The subject is a female aged 40–49; a close-up photograph; the head or neck is involved — 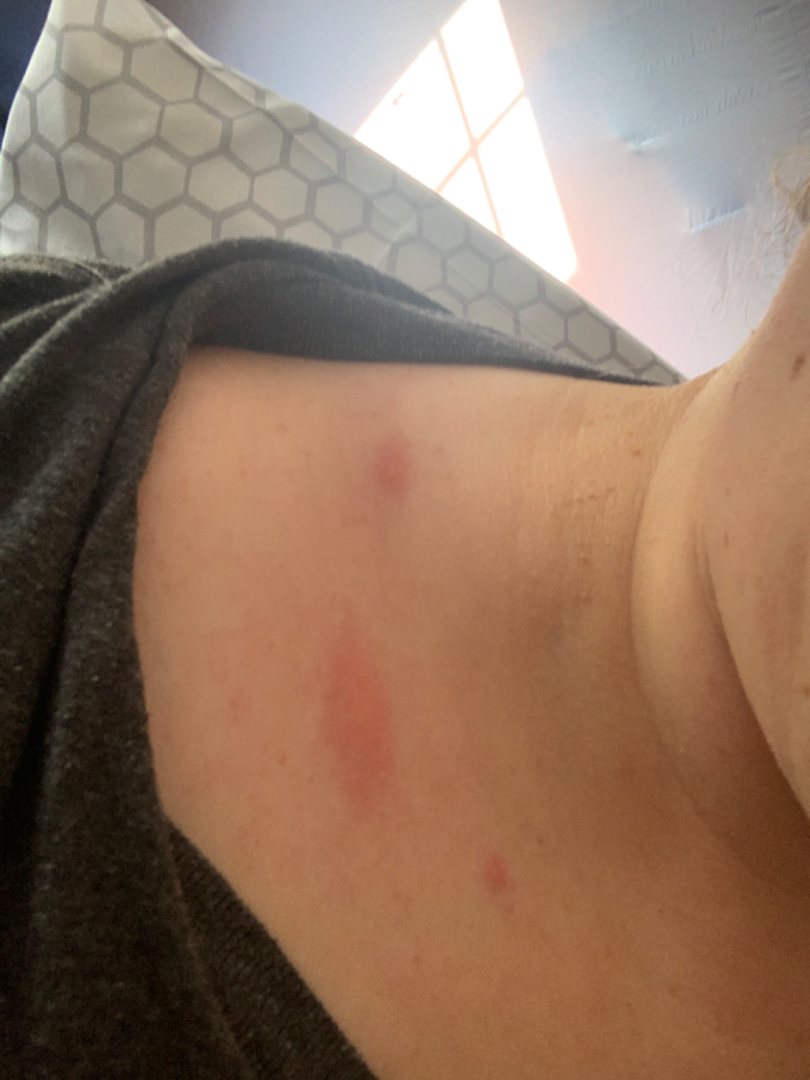Single-reviewer assessment: the impression was split between Urticaria and Insect Bite.